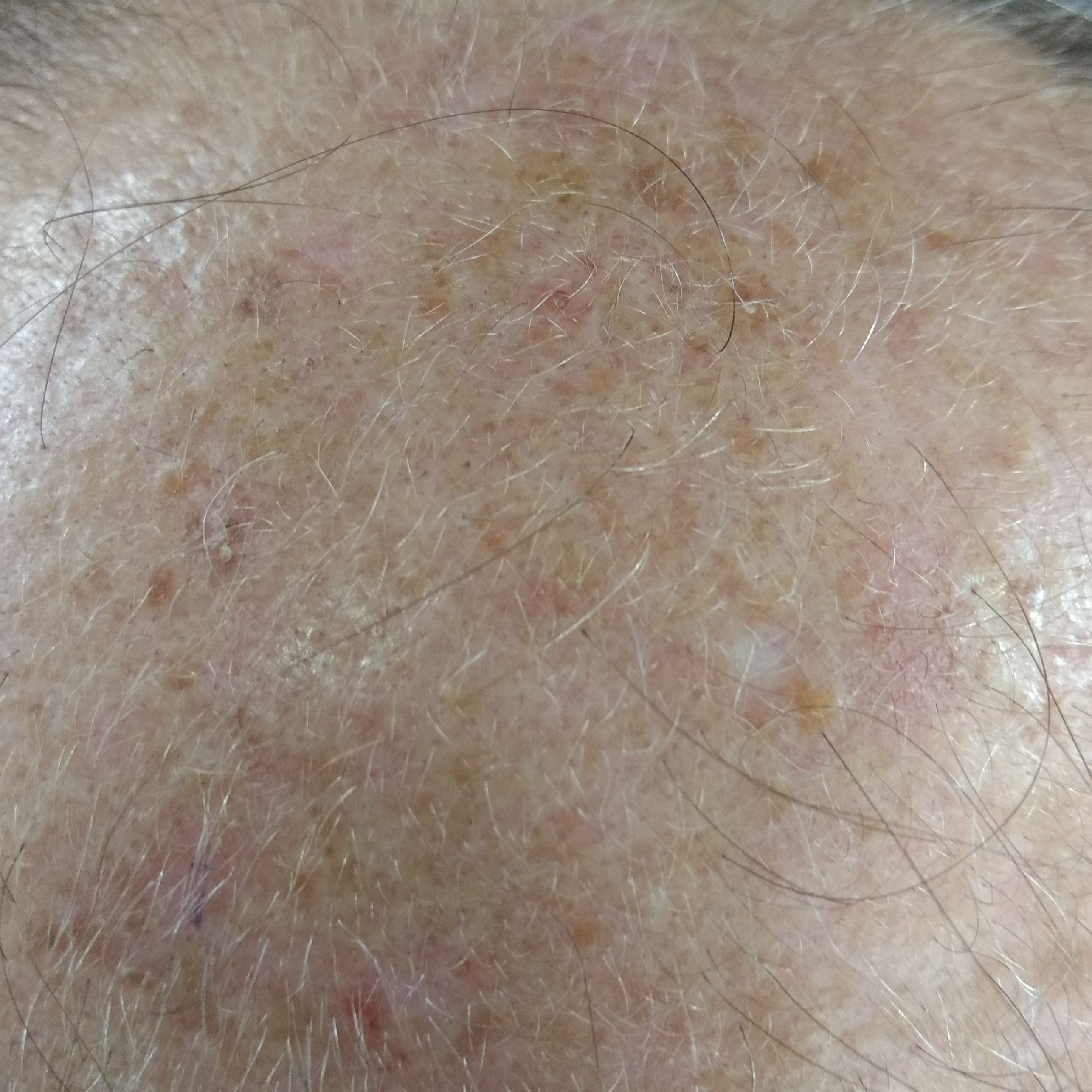patient=male, in their 50s; modality=clinical photograph; skin type=II; reported symptoms=itching; assessment=actinic keratosis (clinical consensus).